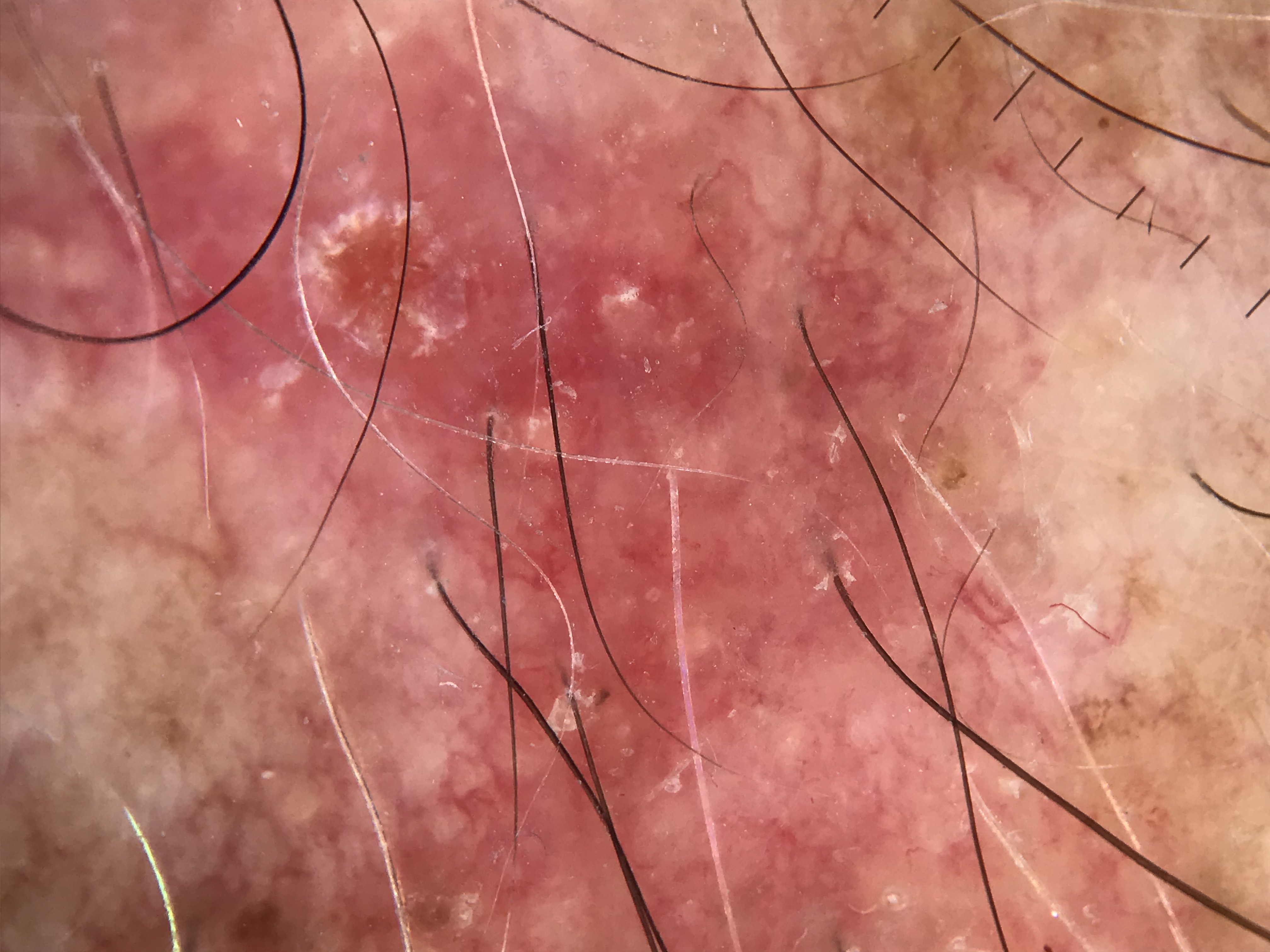Consistent with an actinic keratosis.